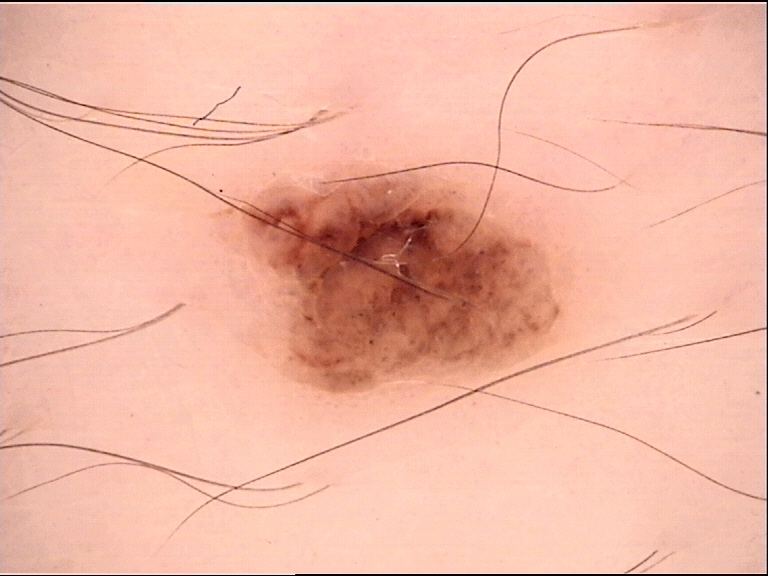Summary:
A dermoscopic image of a skin lesion. This is a banal lesion.
Impression:
The diagnosis was a compound nevus.